The photo was captured at a distance. The back of the torso is involved: 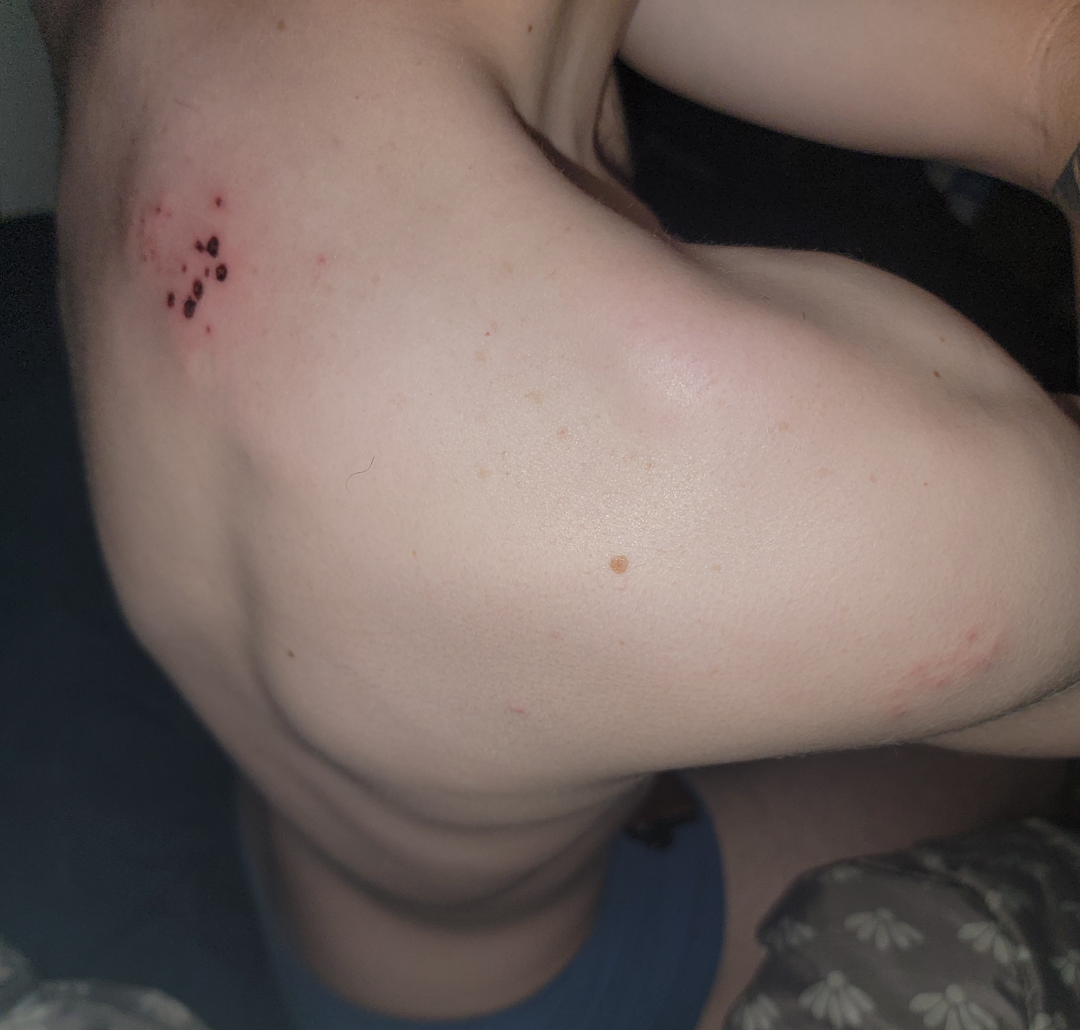{"assessment": "indeterminate from the photograph"}